Close-up view:
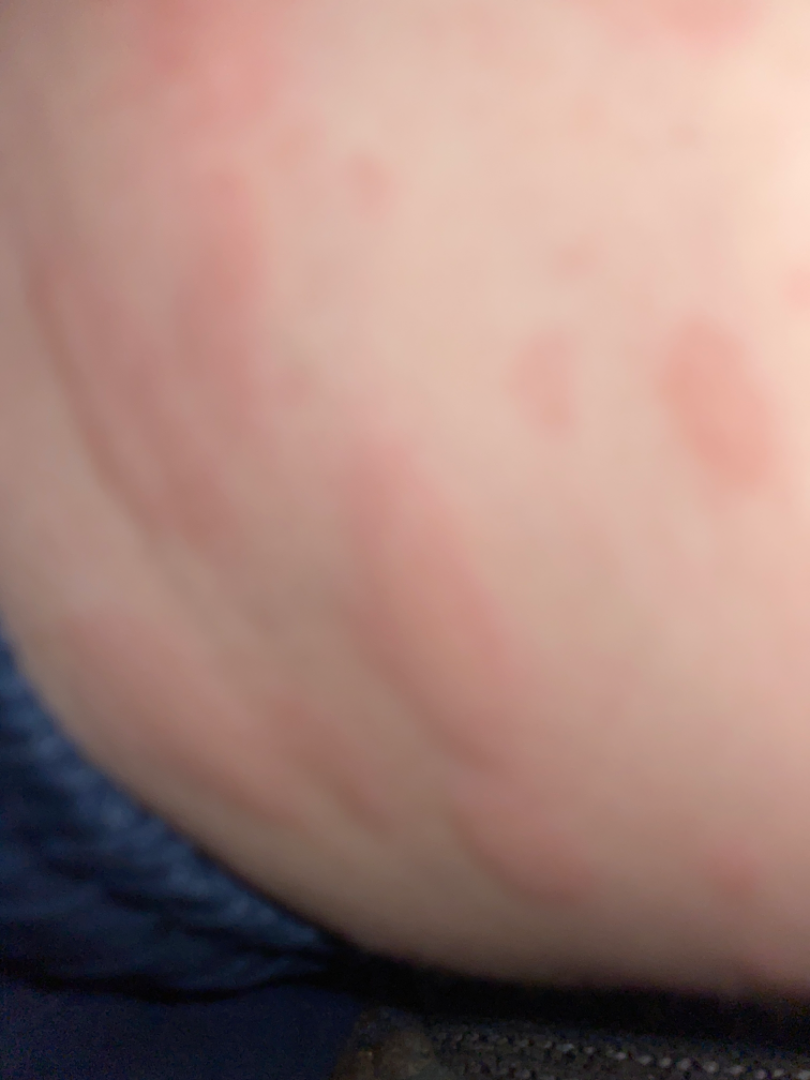The patient notes the lesion is raised or bumpy. No associated systemic symptoms reported. On remote dermatologist review: the impression on review was Urticaria.